A skin lesion imaged with a dermatoscope.
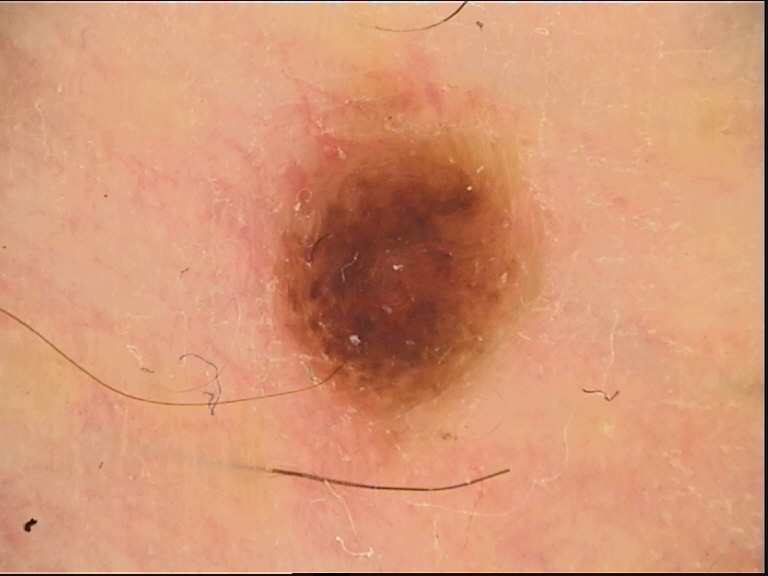class: compound nevus (expert consensus).